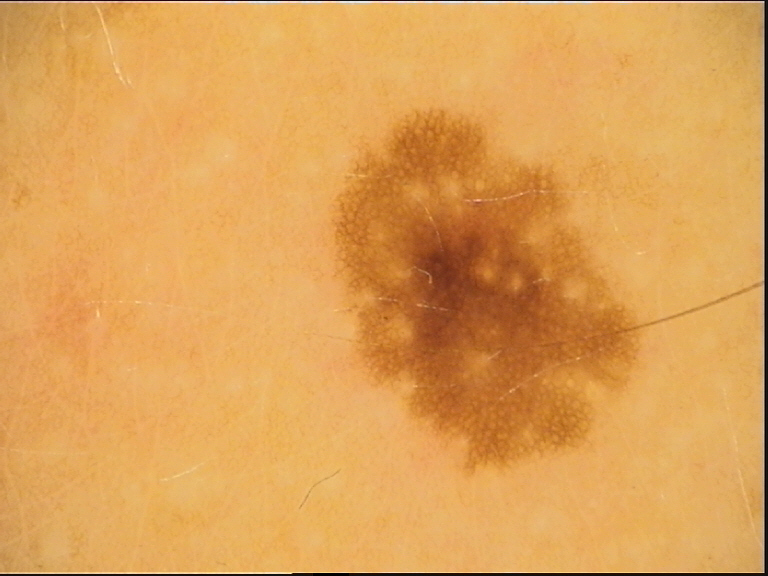image: dermatoscopy; class: dysplastic junctional nevus (expert consensus).